The patient considered this a rash. The patient indicates the lesion is raised or bumpy. Symptoms reported: enlargement, pain, burning and itching. An image taken at a distance. The condition has been present for less than one week. The subject is a female aged 50–59. Skin tone: Fitzpatrick phototype II; lay reviewers estimated MST 2. The head or neck is involved:
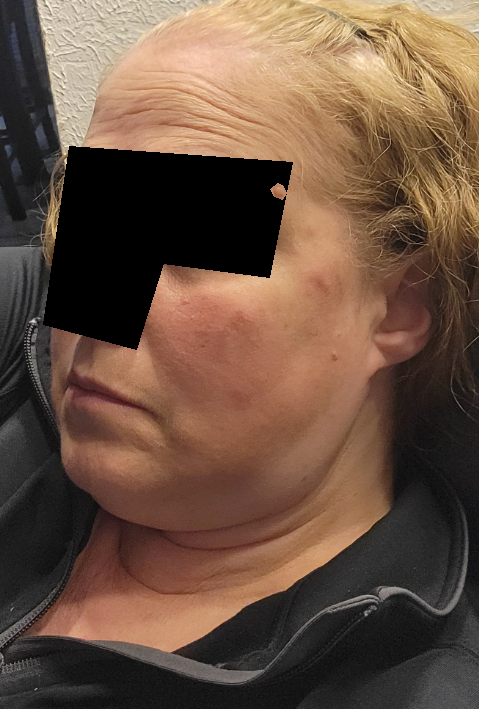<report>
<differential>
  <tied_lead>Rosacea, Allergic Contact Dermatitis, Cutaneous lupus</tied_lead>
</differential>
</report>